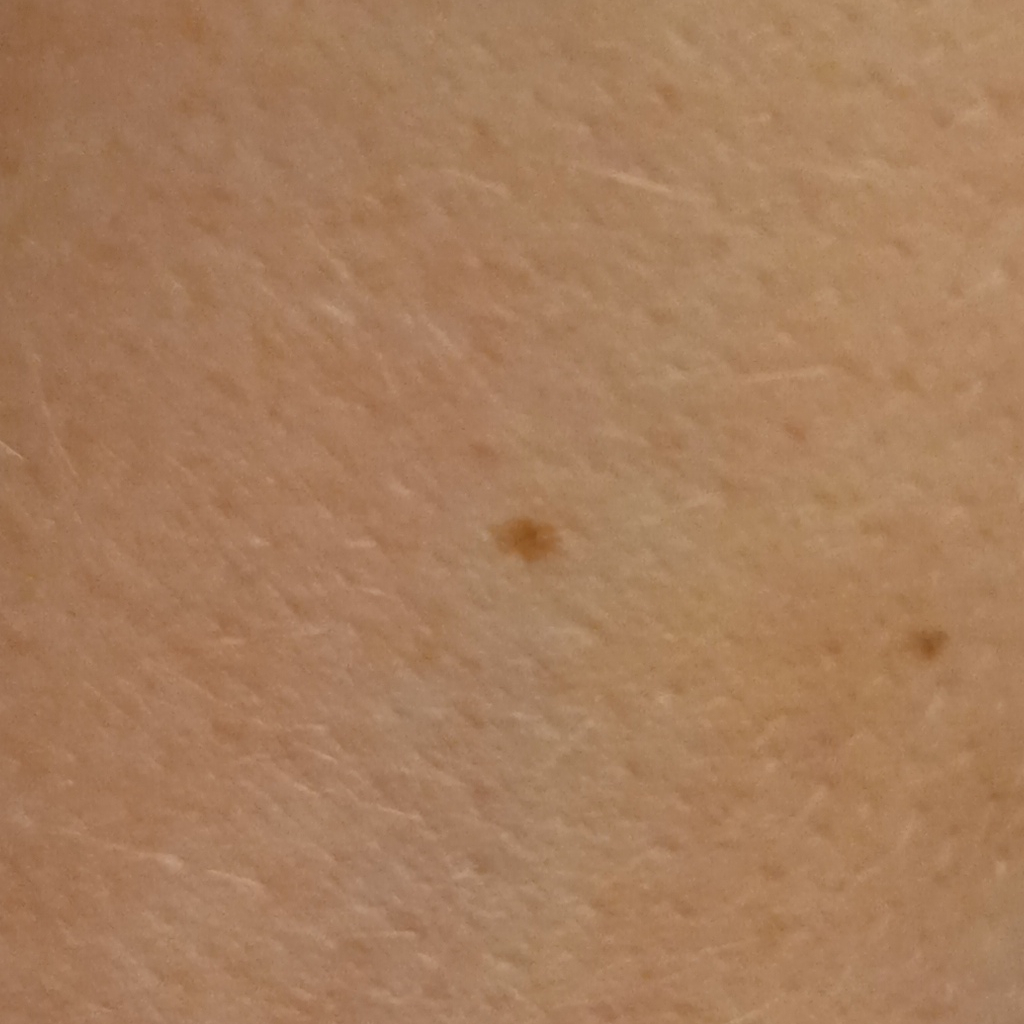Acquired for a research image collection, with no referral diagnosis. A clinical photograph of a skin lesion. A female patient age 50. The lesion measures approximately 2 mm. Dermatologist review favored a melanocytic nevus.